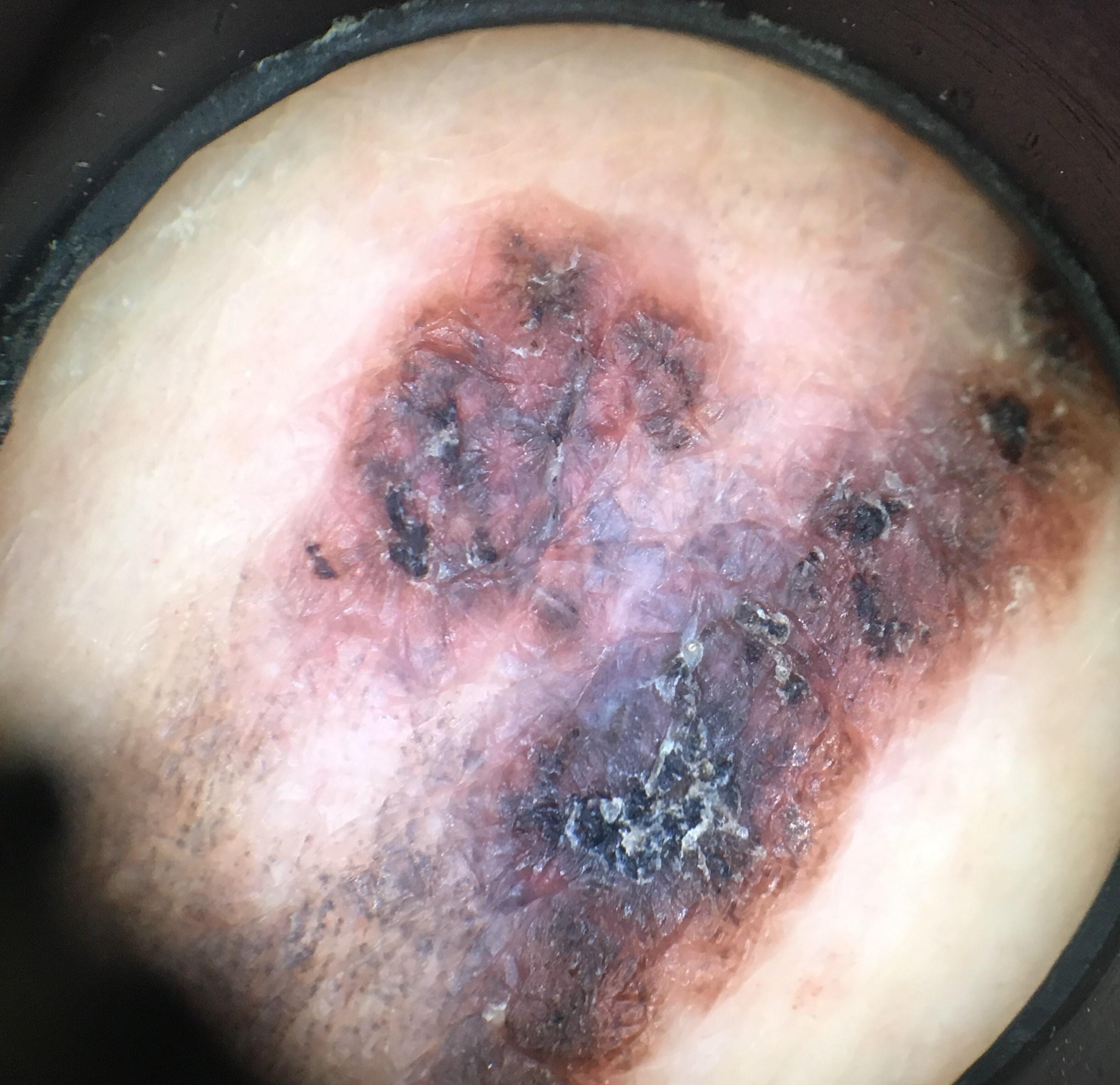  image: dermatoscopic image
  skin_type: II
  lesion_location:
    region: the trunk
    detail: the posterior trunk
  diagnosis:
    name: Melanoma
    malignancy: malignant
    confirmation: histopathology